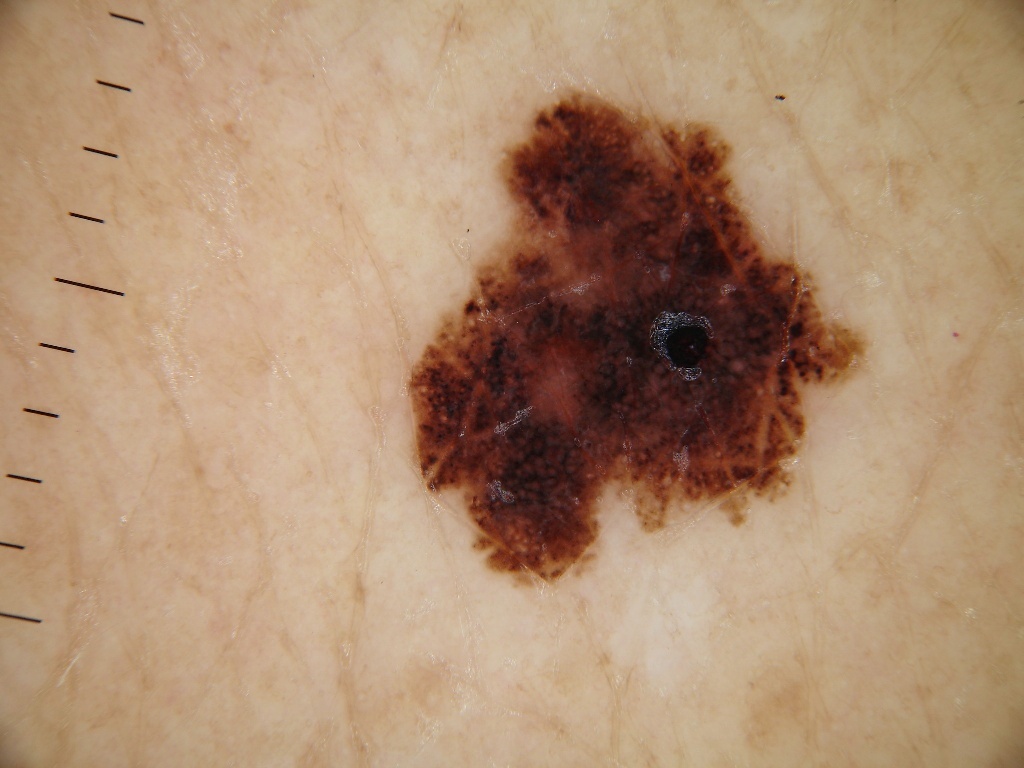Findings:
A dermoscopy image of a single skin lesion. Dermoscopic assessment notes globules and pigment network, with no negative network, streaks, or milia-like cysts. The lesion takes up a moderate portion of the field. As (left, top, right, bottom), the visible lesion spans box(408, 88, 865, 580).
Diagnosis:
Histopathology confirmed a melanoma, a malignancy.